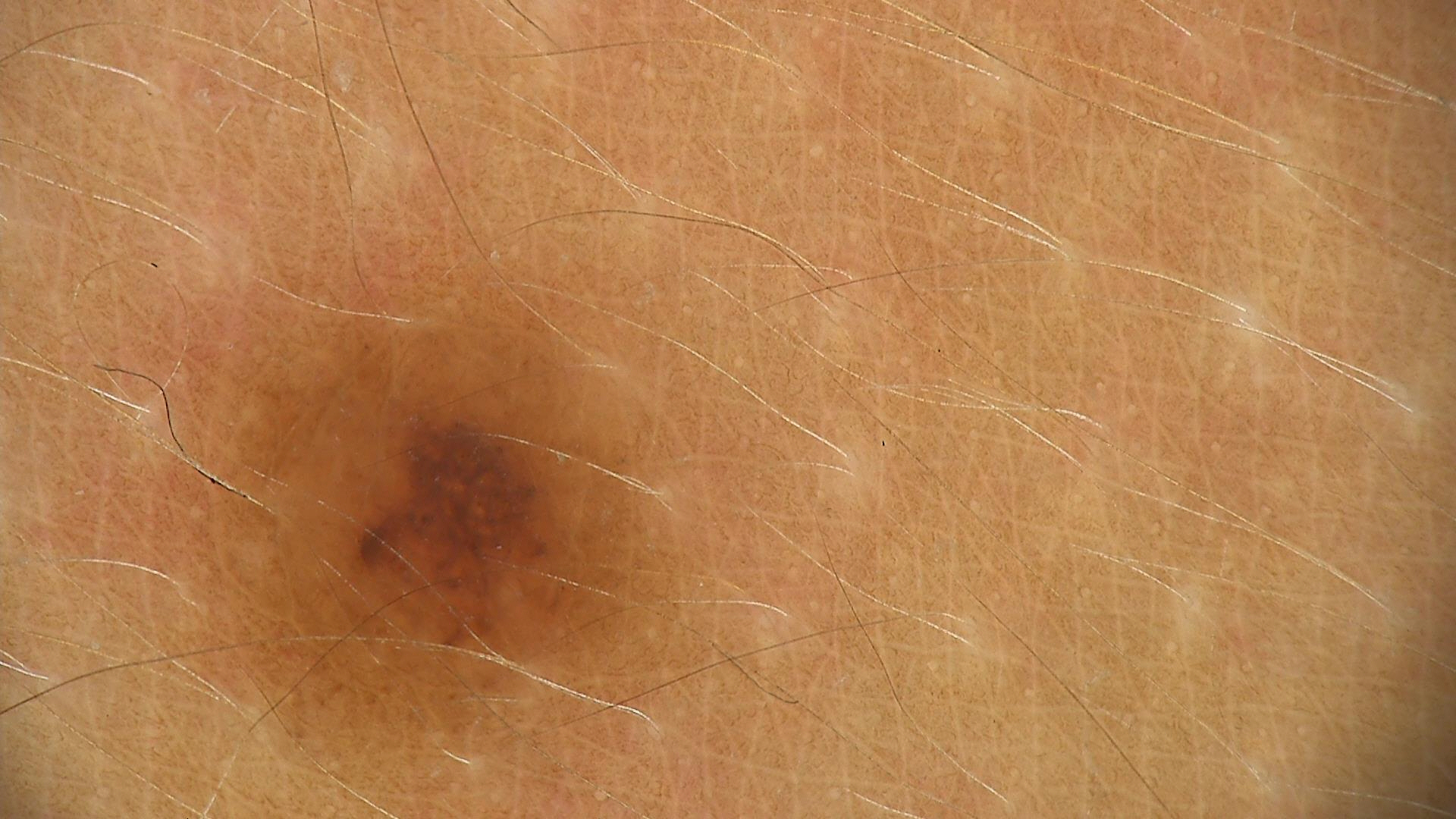image type=dermoscopy | category=banal | class=compound nevus (expert consensus).